A dermoscopy image of a single skin lesion · a male subject aged 68-72: 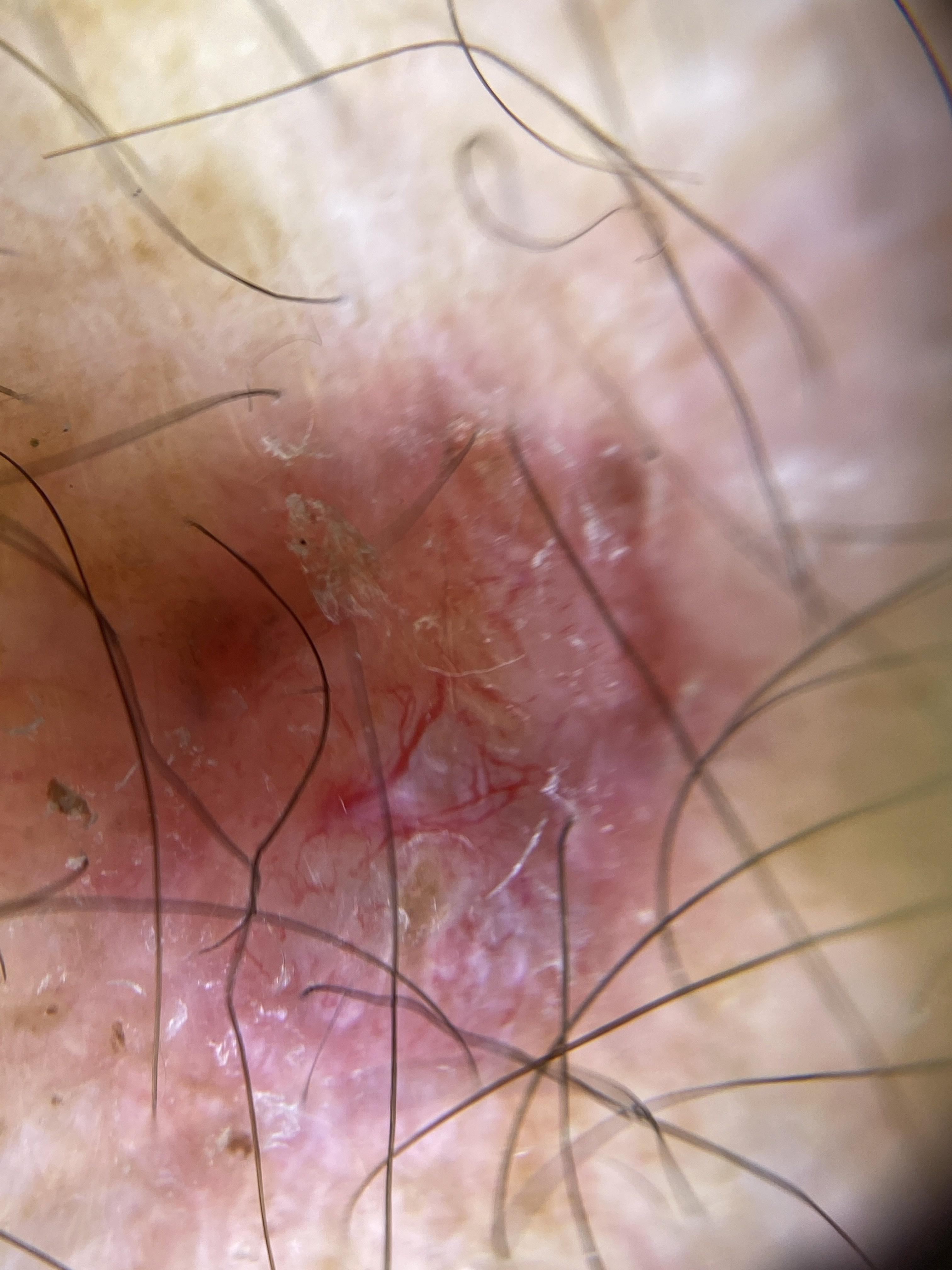Conclusion:
Histopathology confirmed a lesion of adnexal (follicular) origin — a basal cell carcinoma.